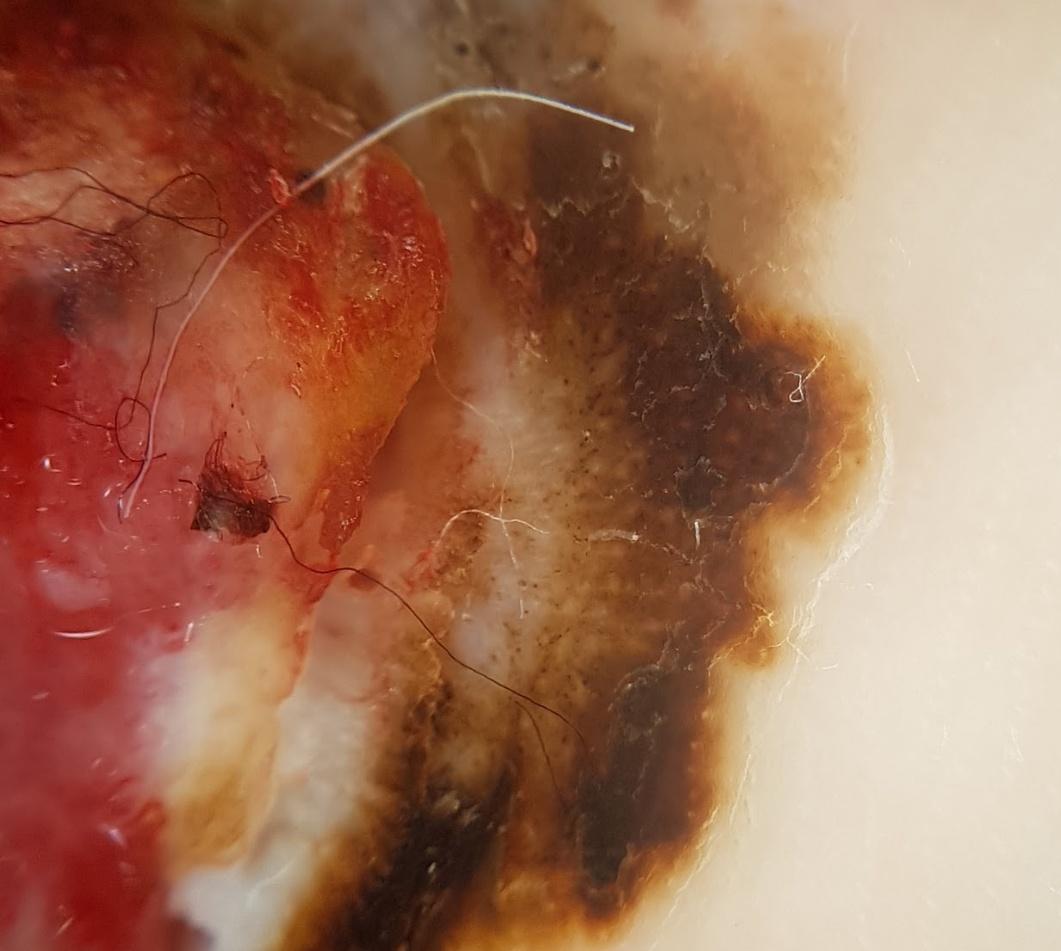Q: What is the melanoma history?
A: a previous melanoma
Q: What kind of image is this?
A: dermatoscopic image
Q: Skin phototype?
A: II
Q: Patient demographics?
A: male, in their mid-60s
Q: Where on the body is the lesion?
A: an acral site (palms or soles)
Q: What is this lesion?
A: Melanoma (biopsy-proven)